A male subject, aged 63-67; a dermoscopy image of a single skin lesion: 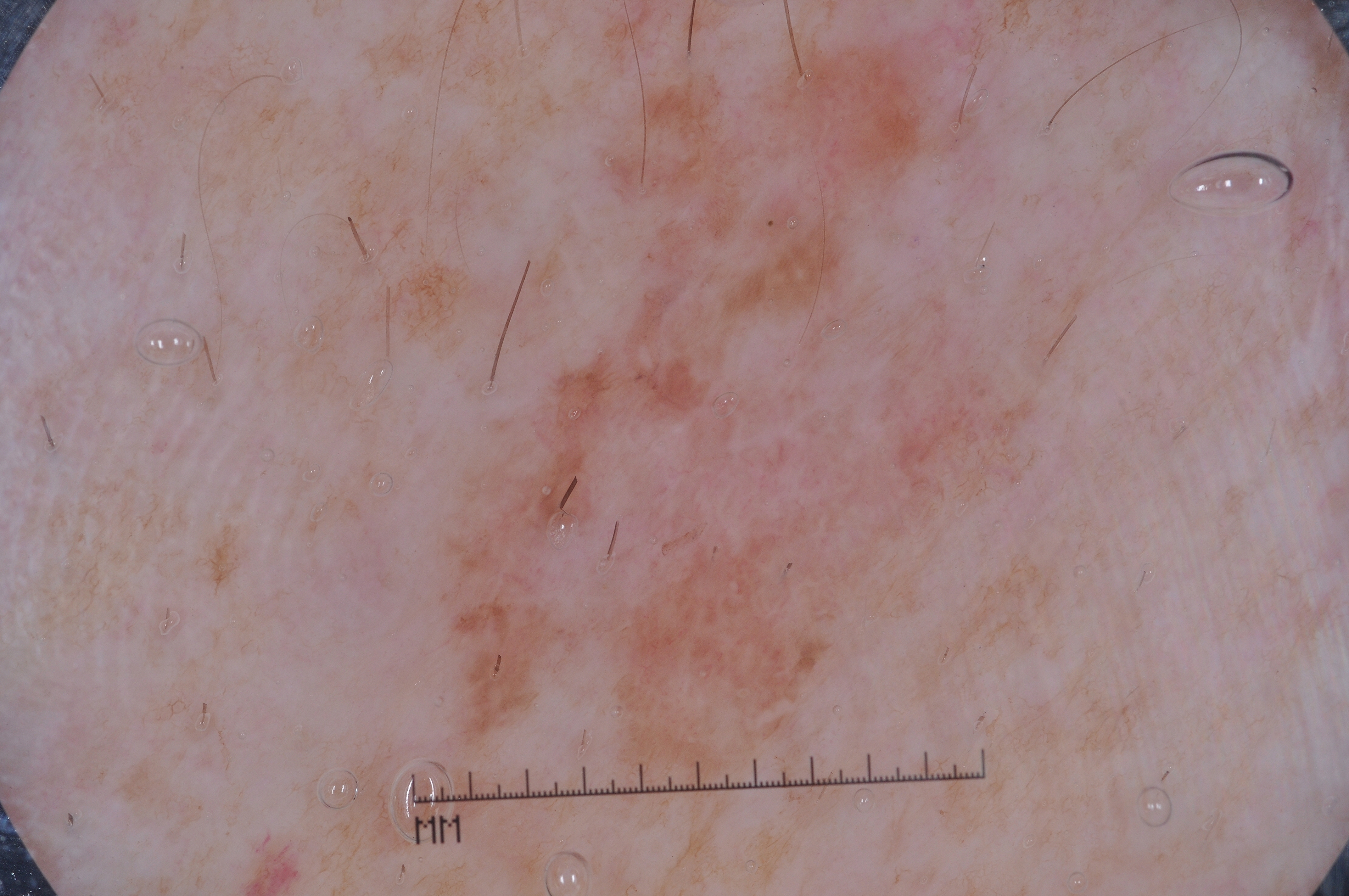Image and clinical context: As (left, top, right, bottom), the lesion spans 274/14/1106/811. On dermoscopy, the lesion shows negative network. A prominent lesion filling much of the field. Conclusion: On biopsy, the diagnosis was a melanoma.